The lesion involves the back of the torso; the subject is 50–59, female; the photo was captured at a distance — 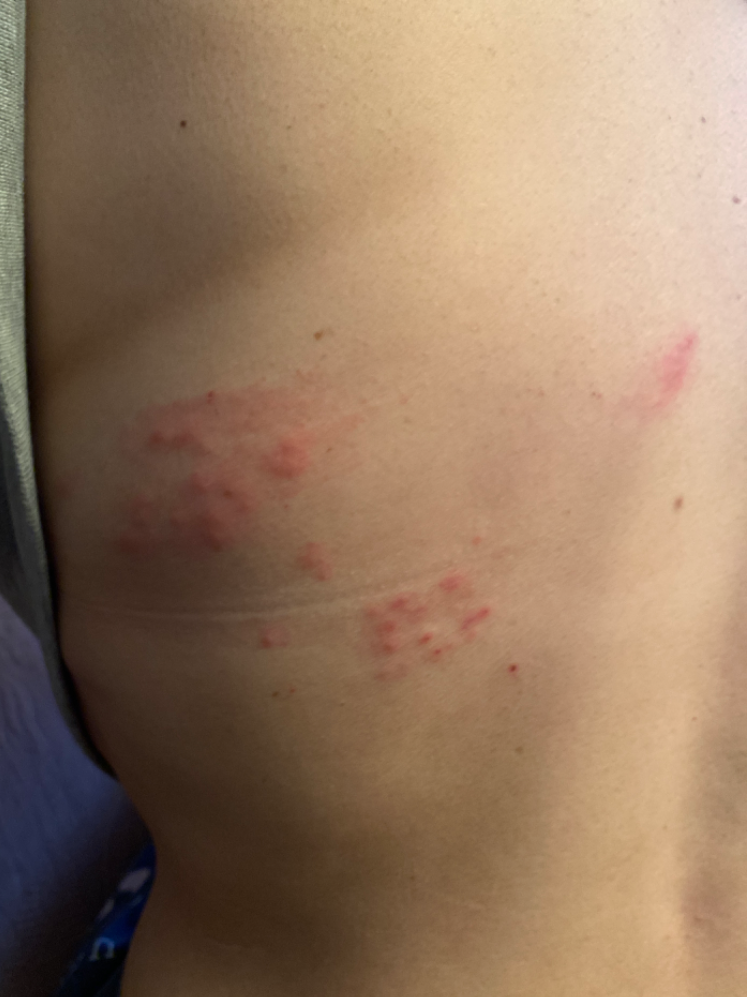A single dermatologist reviewed the case: most likely Herpes Zoster; an alternative is Allergic Contact Dermatitis; possibly Herpes Simplex.